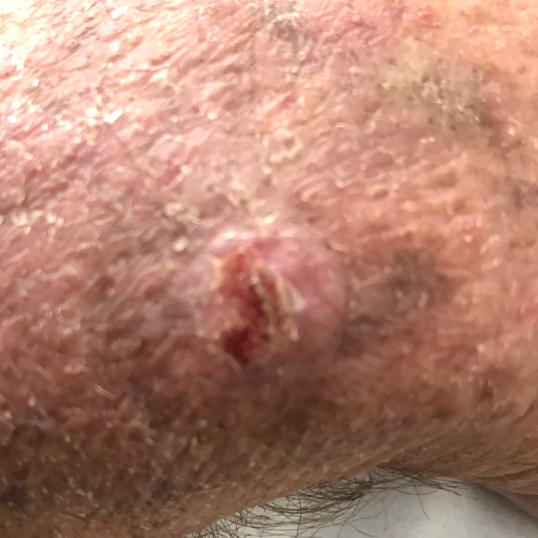A clinical photograph of a skin lesion. The lesion is located on a forearm. Per patient report, the lesion has bled, is elevated, itches, and hurts. Confirmed on histopathology as a basal cell carcinoma.